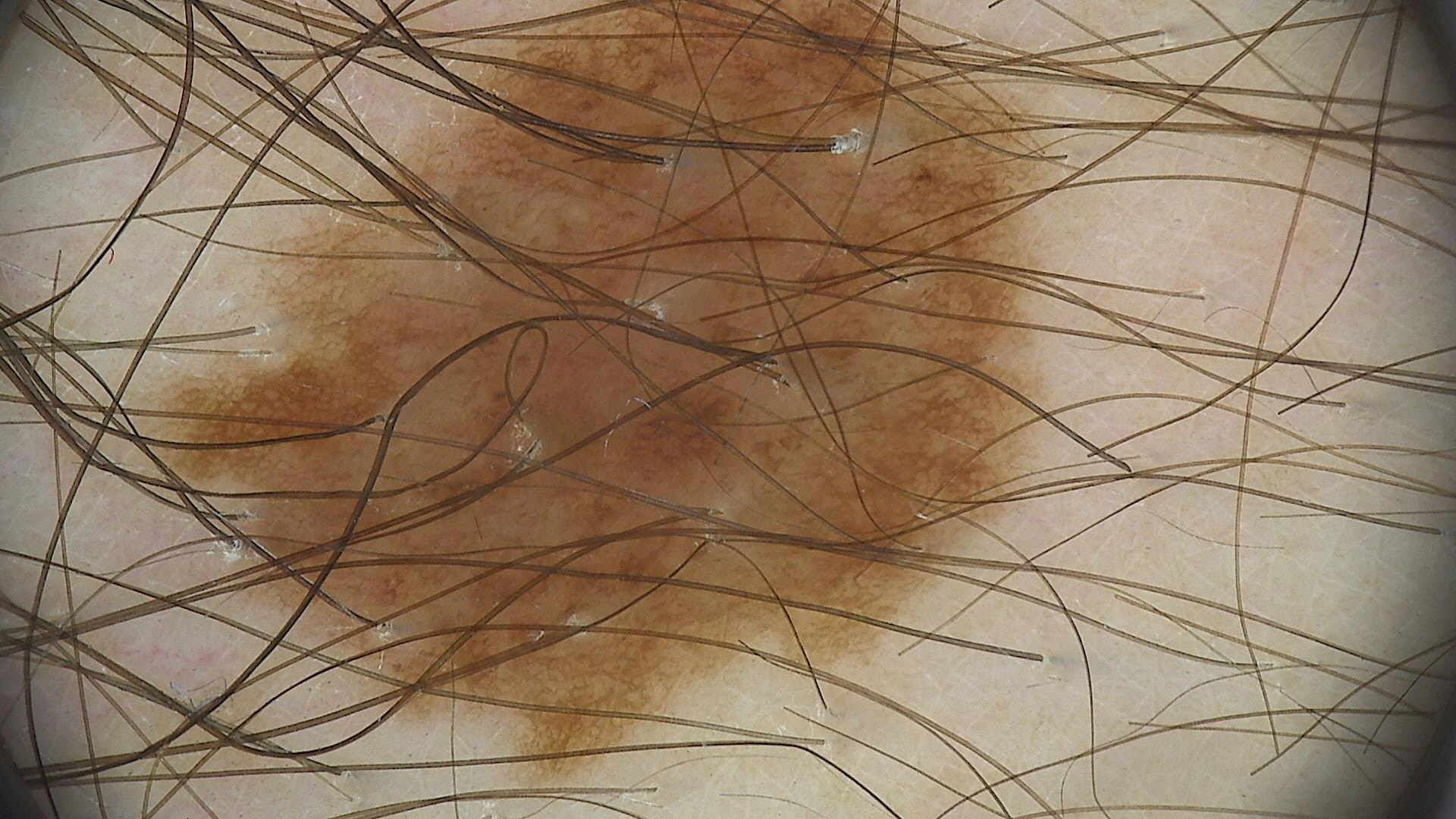image type=dermatoscopy
label=dysplastic junctional nevus (expert consensus)